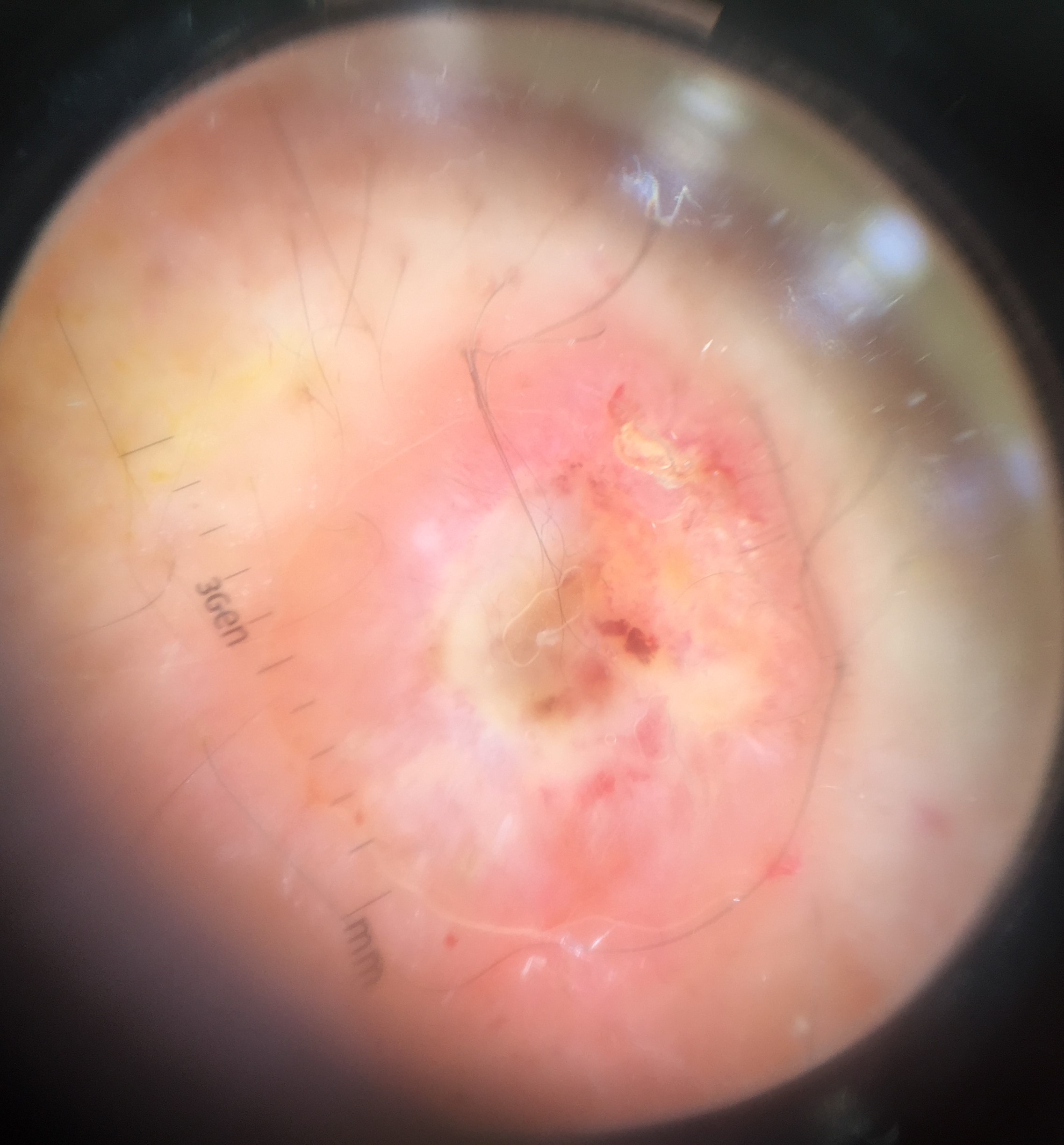A dermoscopic close-up of a skin lesion. The biopsy diagnosis was a malignant, keratinocytic lesion — a squamous cell carcinoma.